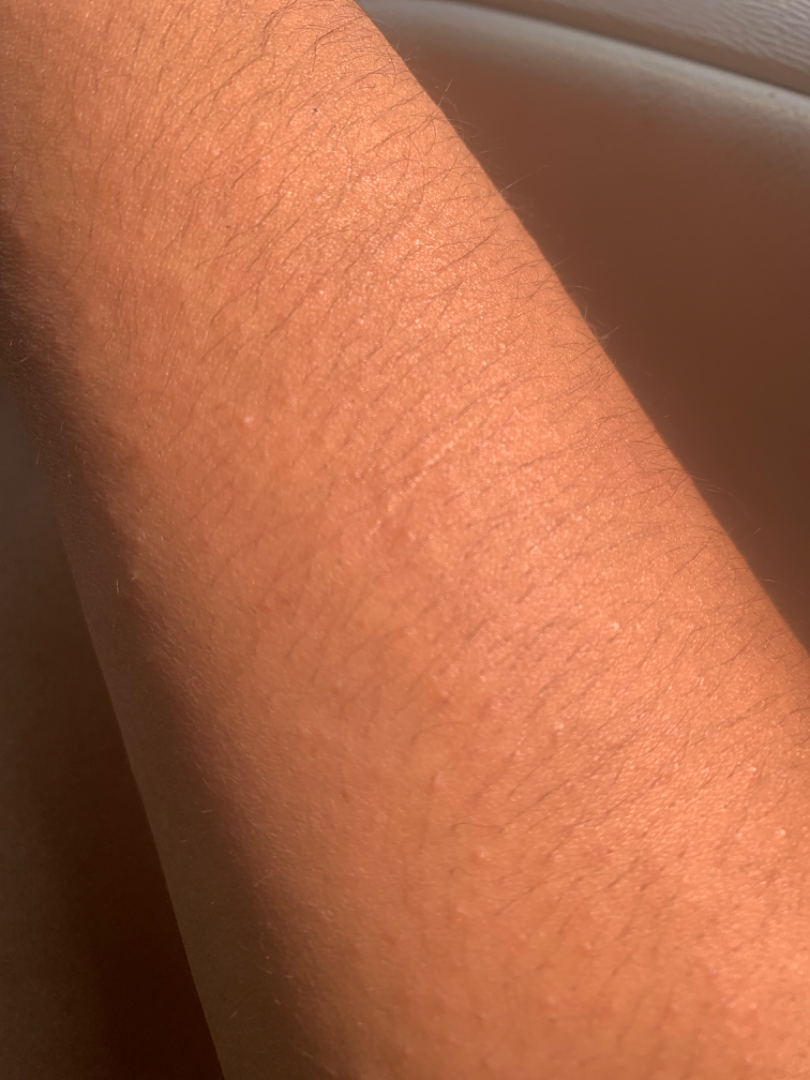{"duration": "less than one week", "patient_category": "a rash", "texture": "raised or bumpy", "shot_type": "close-up", "symptoms": "itching", "body_site": "arm", "patient": "female, age 18–29", "systemic_symptoms": "mouth sores", "differential": {"Keratosis pilaris": 0.41, "Acute dermatitis, NOS": 0.22, "Folliculitis": 0.18, "Eczema": 0.18}}